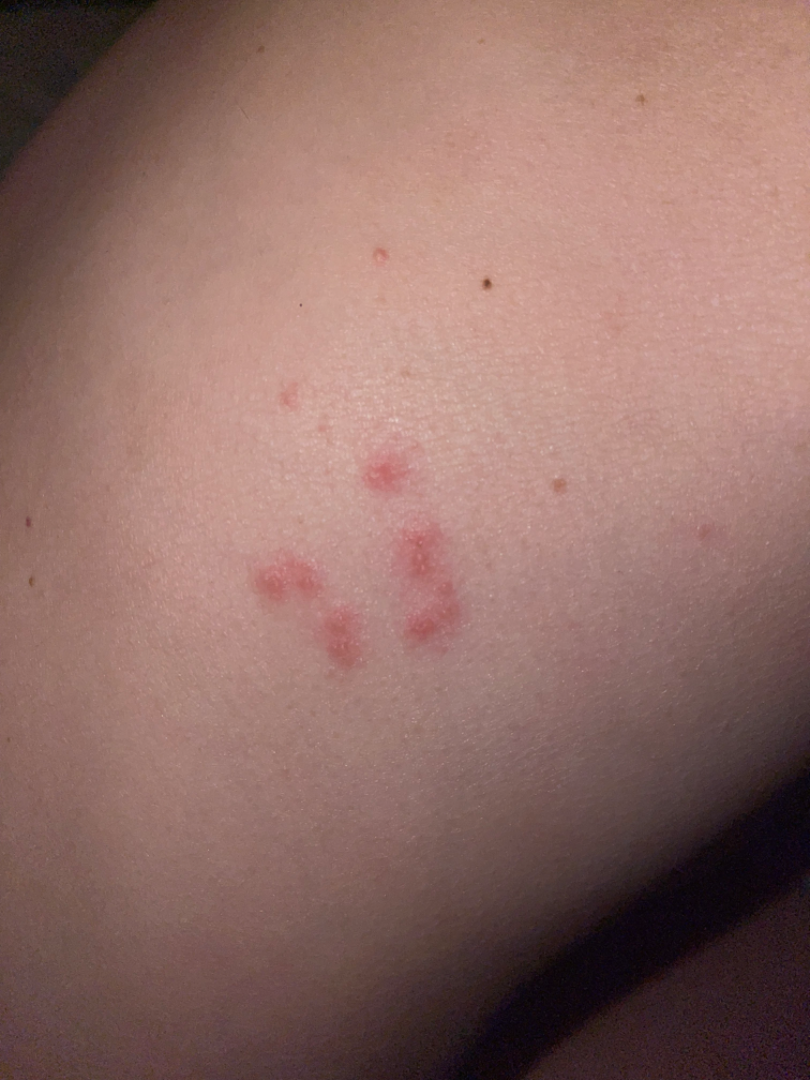An image taken at a distance. The back of the torso is involved. On remote dermatologist review: Herpes Zoster (100%).